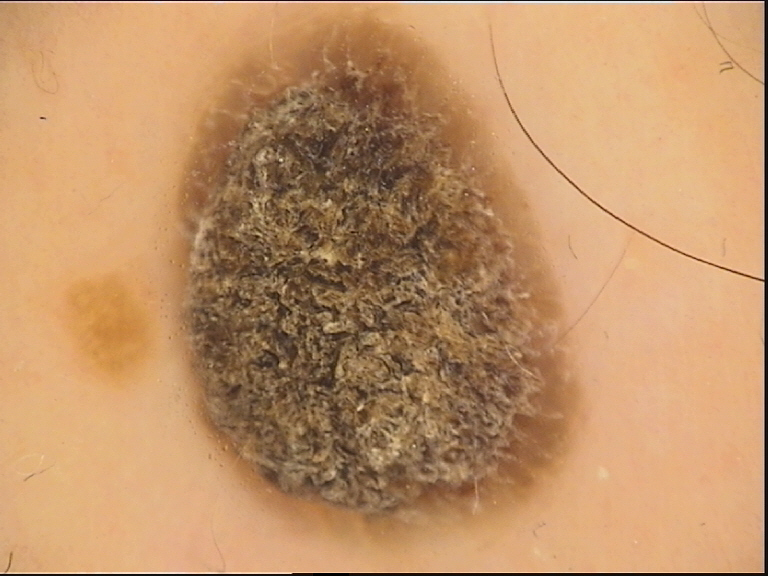Case: Dermoscopy of a skin lesion. Impression: Diagnosed as a keratinocytic lesion — a seborrheic keratosis.